The patient notes the condition has been present for less than one week · the lesion is described as flat · the patient is 18–29, male · close-up view · located on the arm · no constitutional symptoms were reported — 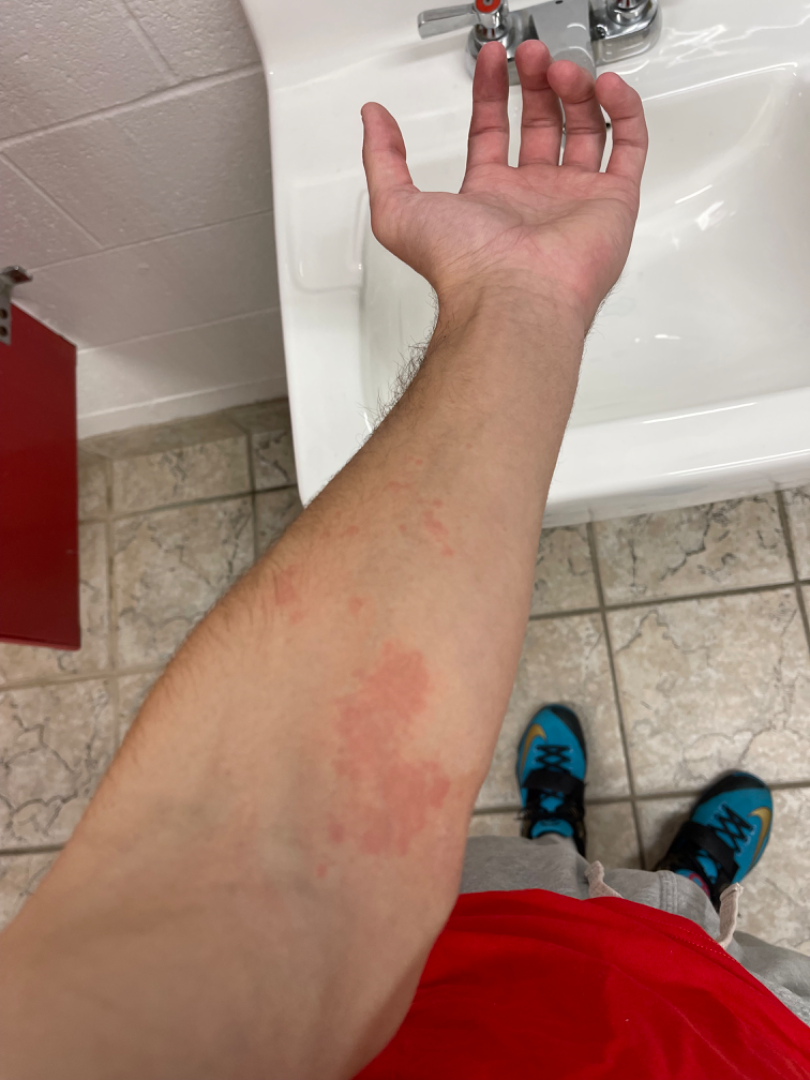Q: What is the dermatologist's impression?
A: Allergic Contact Dermatitis (55%); Urticaria (27%); Abrasion, scrape, or scab (18%)